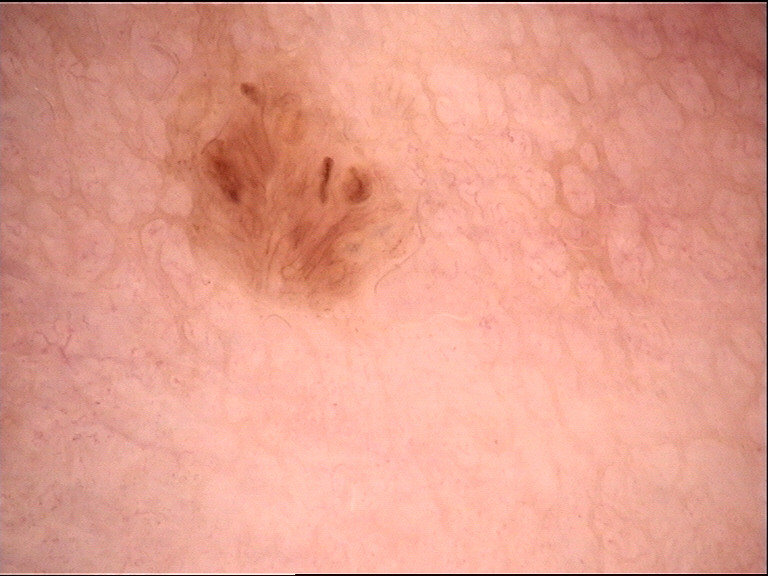Impression: The diagnosis was a dermal nevus.